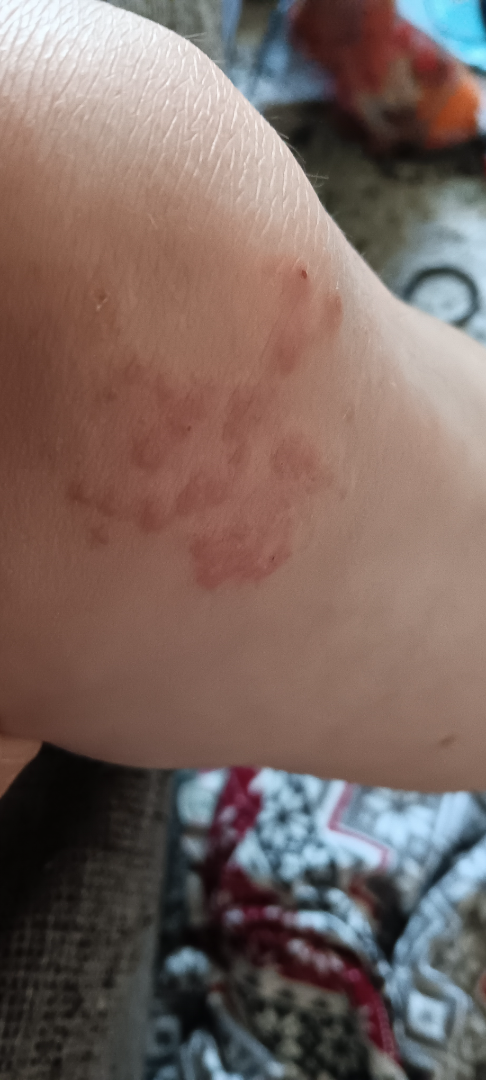skin tone=Fitzpatrick II | contributor=female, age 18–29 | patient-reported symptoms=bothersome appearance and enlargement | self-categorized as=a rash | onset=one to four weeks | location=leg | image framing=at an angle | other reported symptoms=joint pain and fatigue | surface texture=raised or bumpy | clinical impression=Psoriasis (51%); Verruca vulgaris (21%); Dermatitis herpetiformis (19%); Eczema (9%).